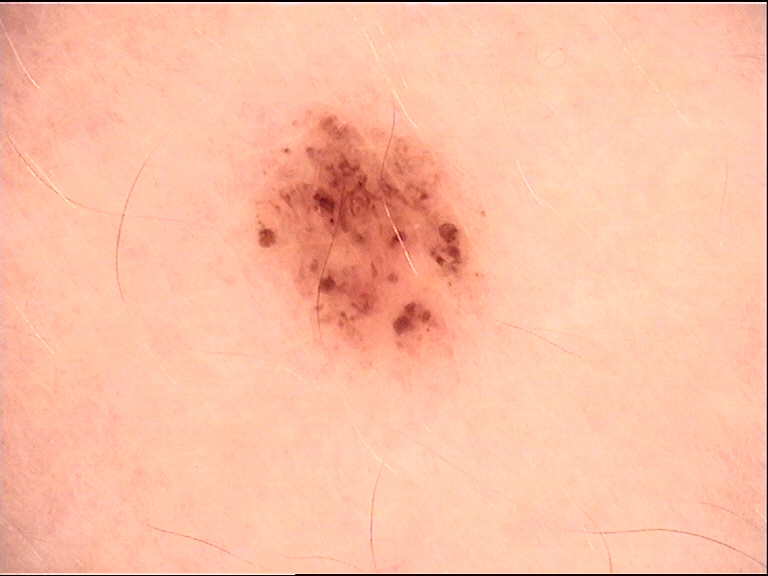| key | value |
|---|---|
| diagnostic label | dysplastic junctional nevus (expert consensus) |